A dermoscopic image of a skin lesion:
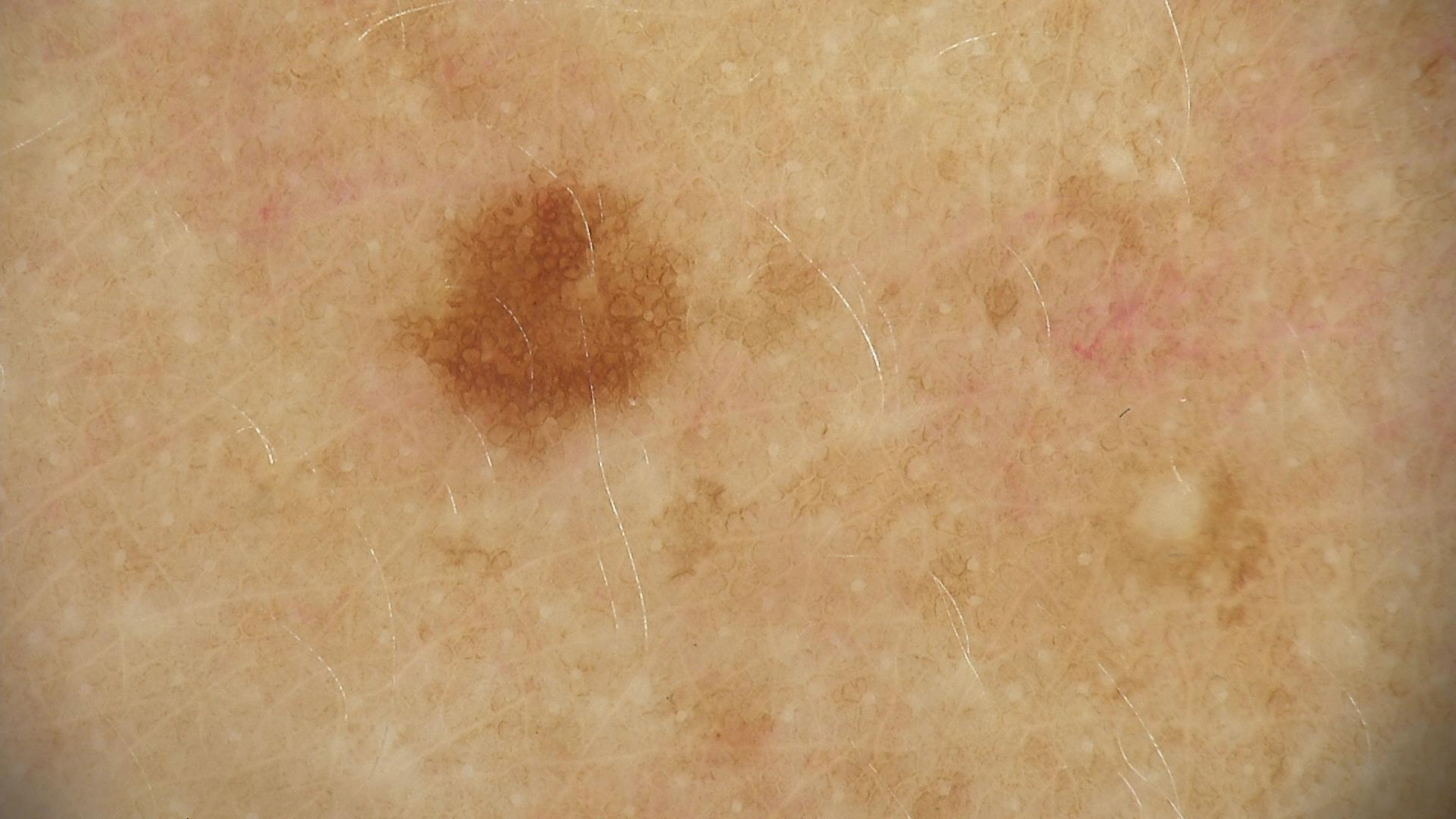Labeled as a benign lesion — a dysplastic junctional nevus.